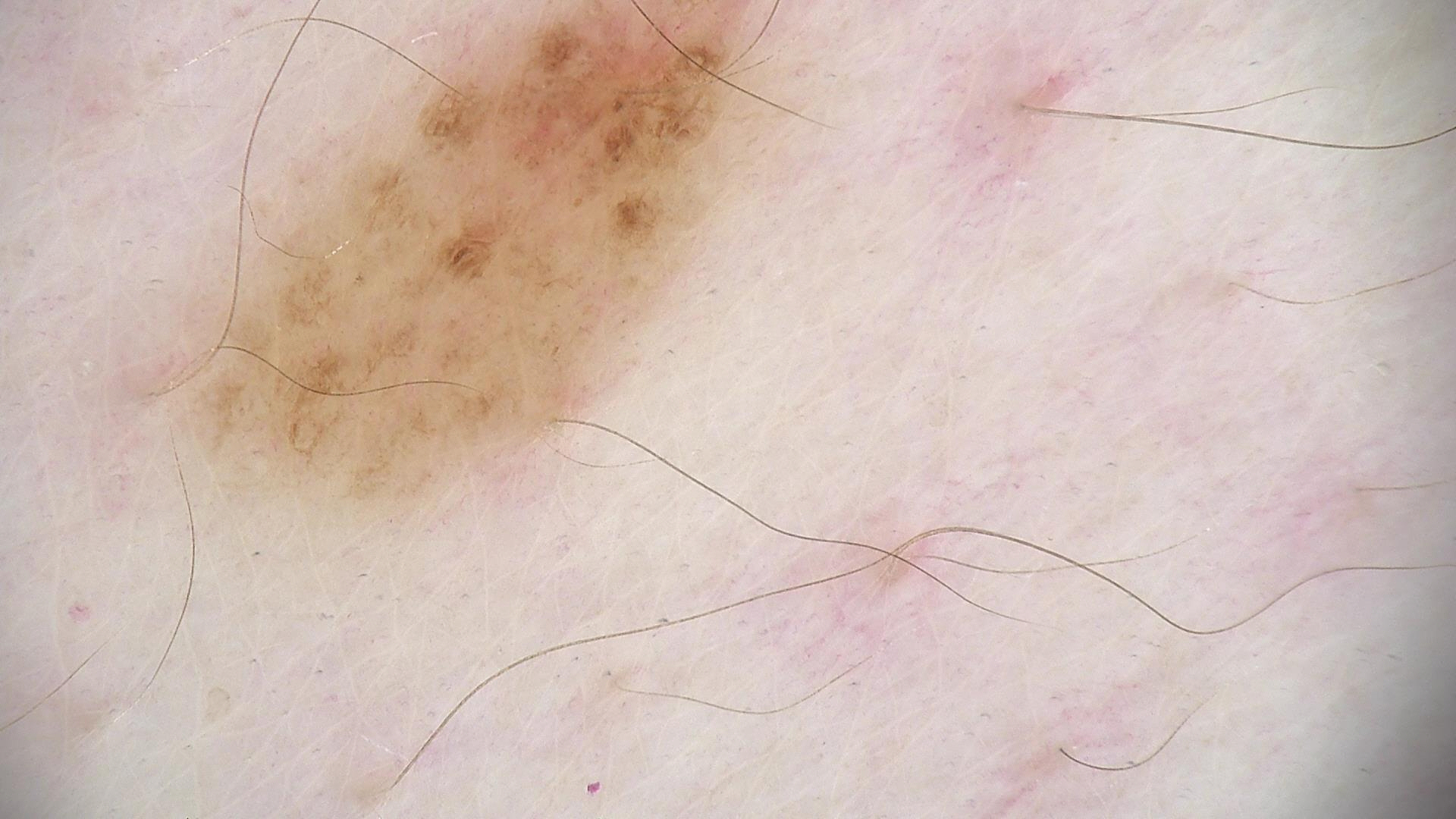Diagnosed as a benign lesion — a dysplastic junctional nevus.